A female patient, about 50 years old; a dermoscopy image of a single skin lesion — 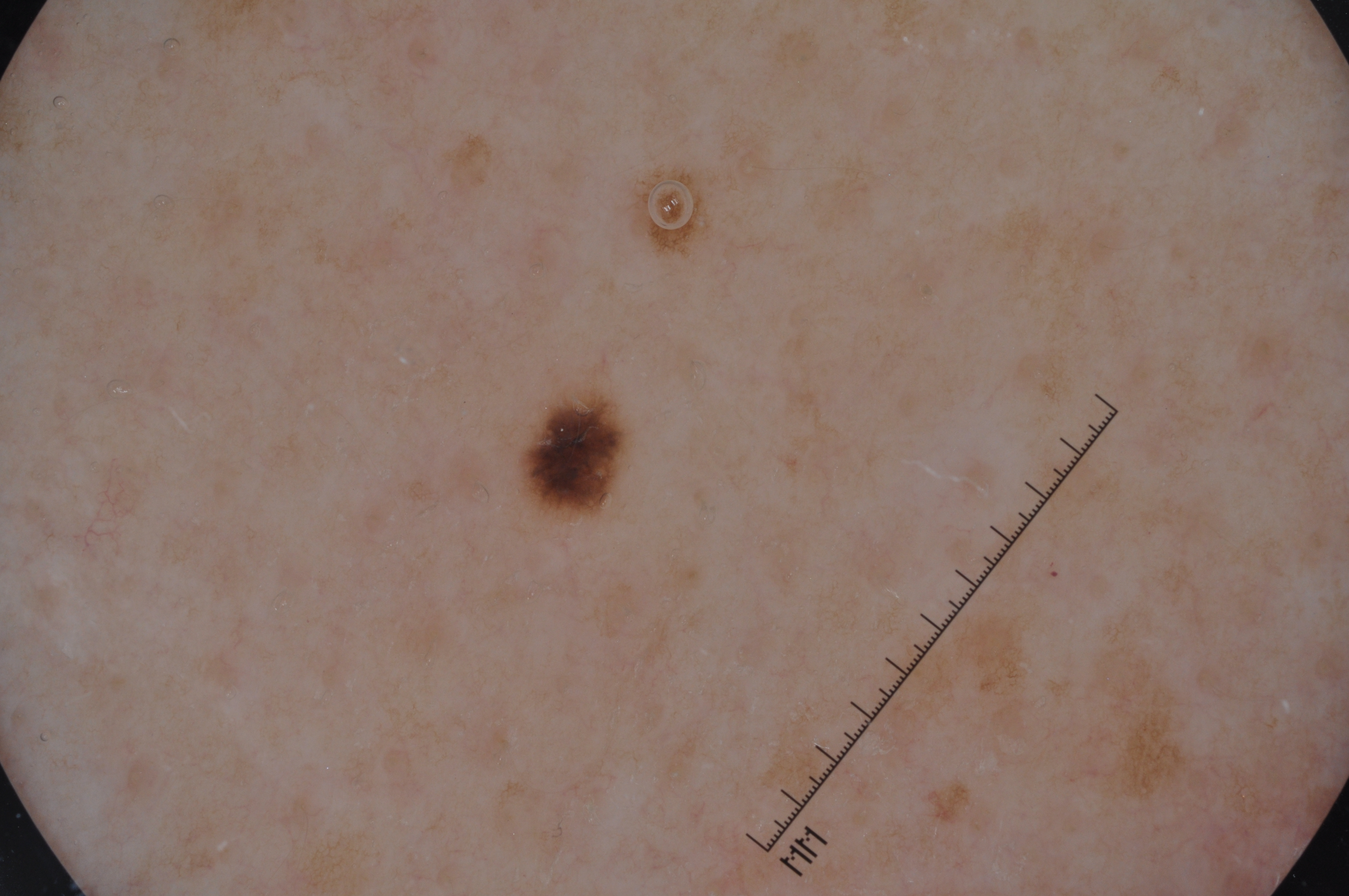Dermoscopic assessment notes pigment network. As (left, top, right, bottom), lesion location: [517,387,631,519]. The lesion occupies roughly 1% of the field. The diagnostic assessment was a melanocytic nevus, a benign lesion.